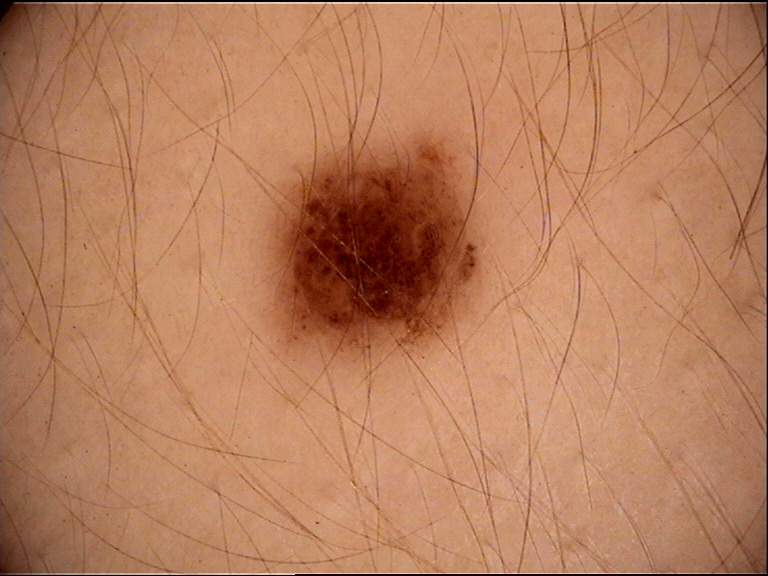A dermatoscopic image of a skin lesion. The architecture is that of a banal lesion. Classified as a junctional nevus.